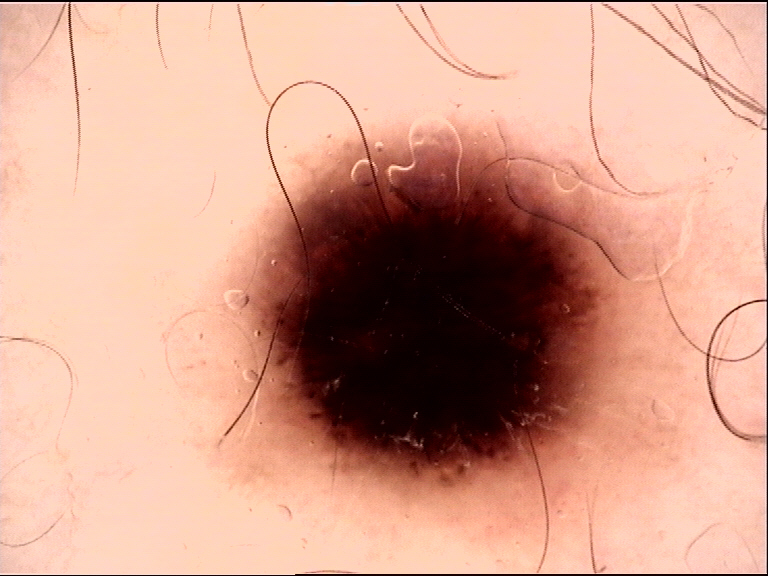The diagnosis was a dysplastic compound nevus.